The patient says their skin tans without first burning; acquired for a research image collection, with no referral diagnosis; a female patient 67 years old; the patient reports no sunbed use and no family history of skin cancer; the patient describes having few moles overall:
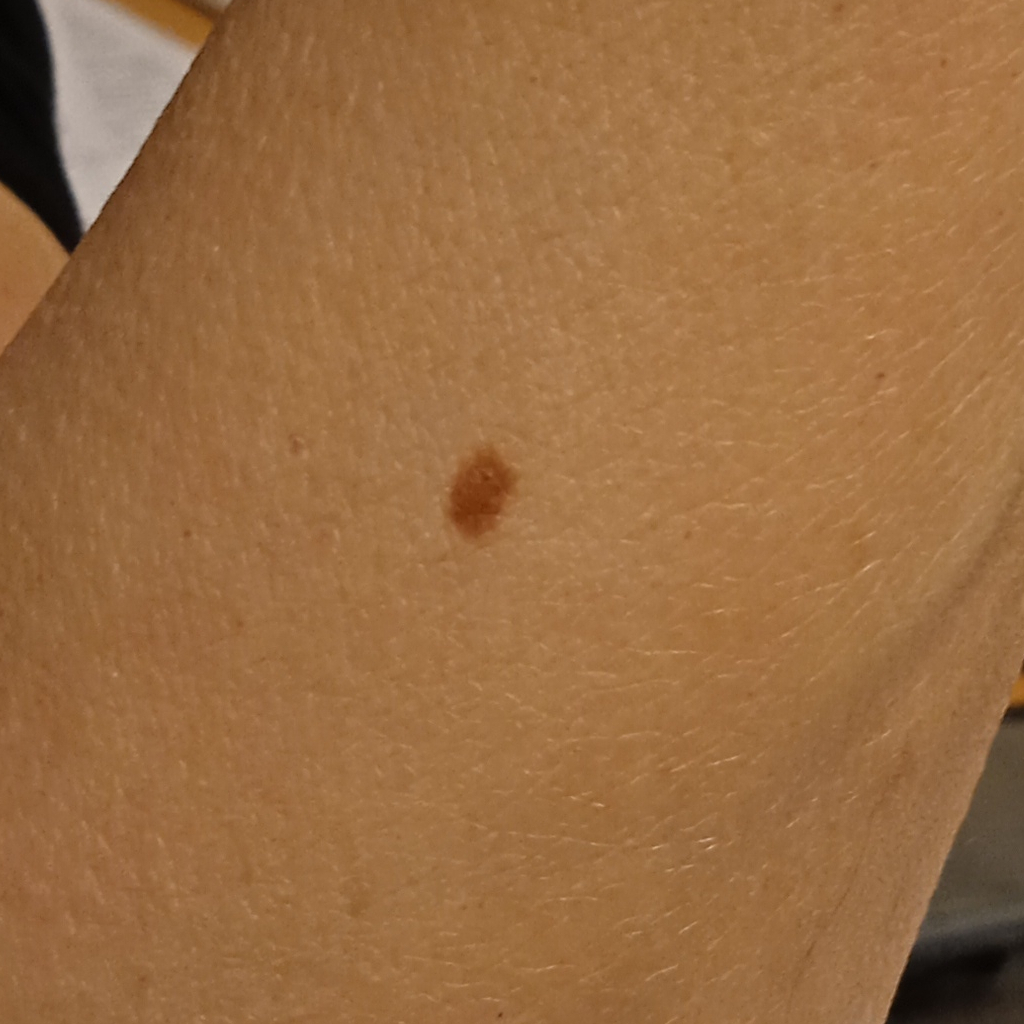  lesion_location: an arm
  lesion_size:
    diameter_mm: 4.9
  diagnosis:
    name: melanocytic nevus
    malignancy: benign